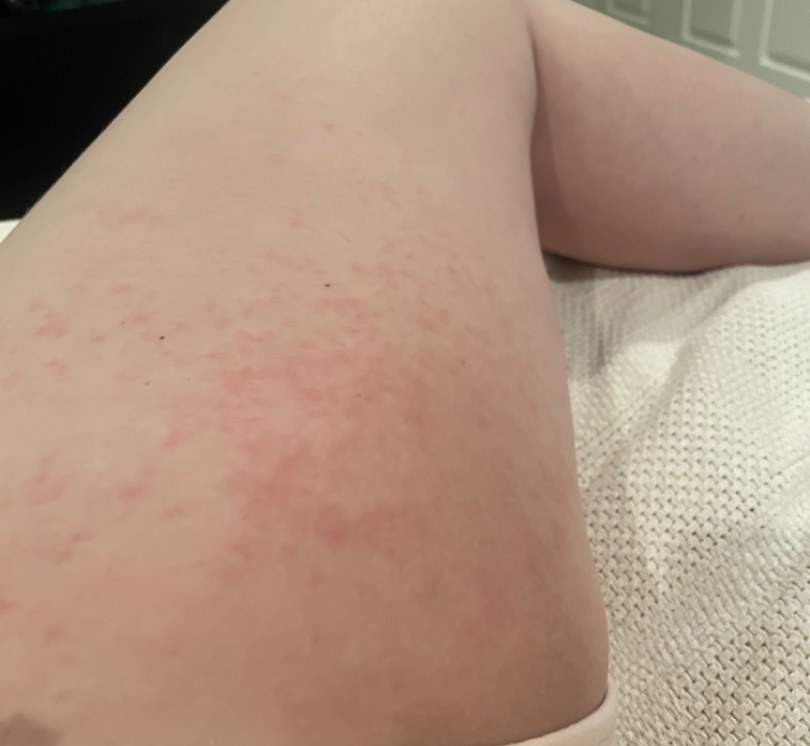The subject is 18–29, female.
The patient reports itching.
The leg and arm are involved.
The patient described the issue as a rash.
Texture is reported as raised or bumpy.
The photo was captured at an angle.
The patient reports the condition has been present for less than one week.
No constitutional symptoms were reported.
On teledermatology review: Eczema (possible); Allergic Contact Dermatitis (possible); Drug Rash (possible).